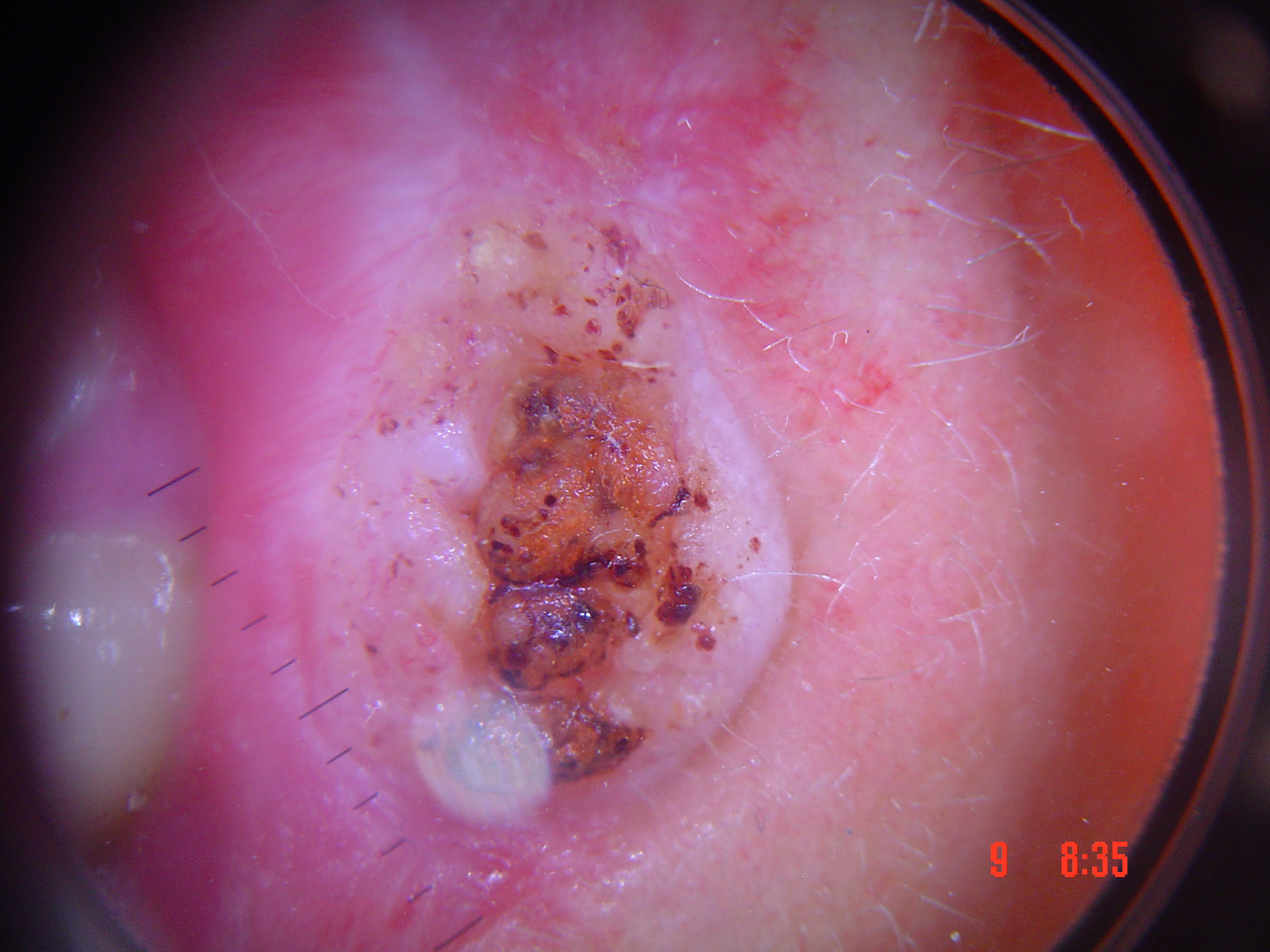Conclusion: Confirmed on histopathology as a squamous cell carcinoma.